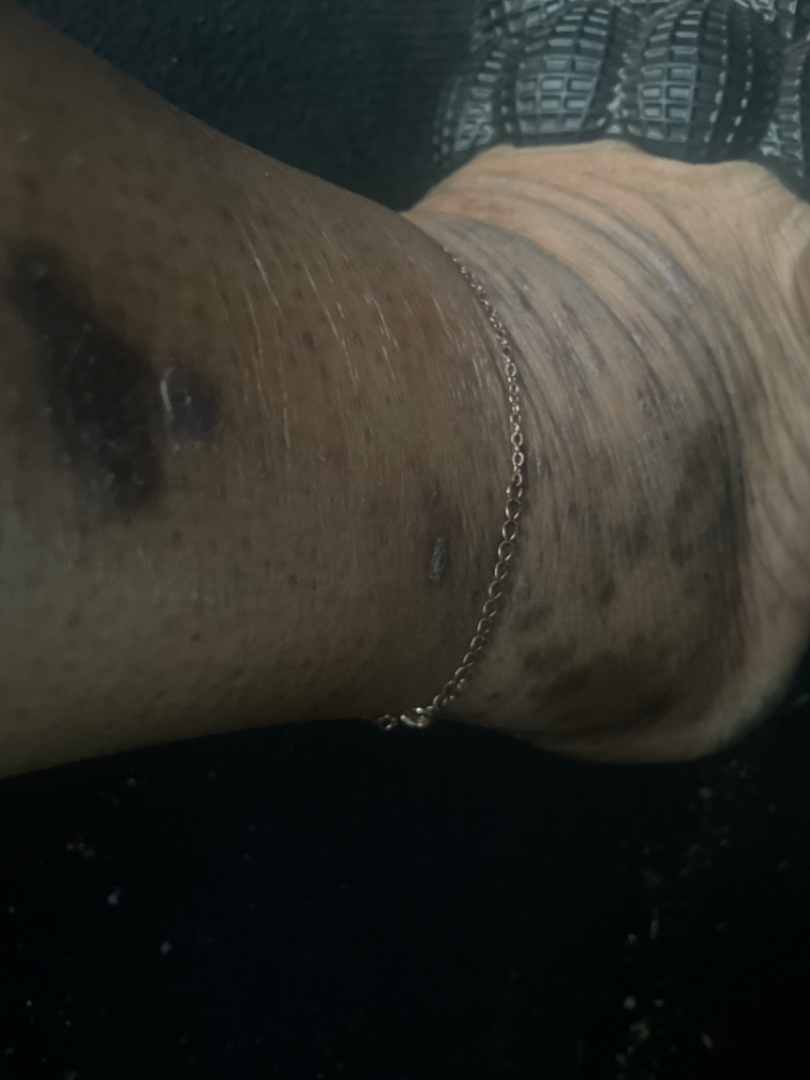Associated systemic symptoms include fatigue. The patient described the issue as a rash. The arm and top or side of the foot are involved. Present for three to twelve months. The patient notes bothersome appearance, darkening and itching. Close-up view. Most consistent with Lichen planus/lichenoid eruption.